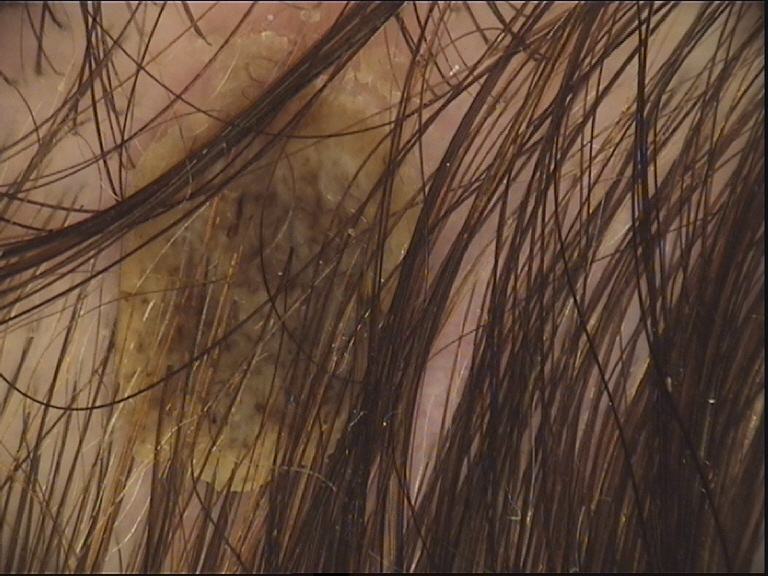The architecture is that of a keratinocytic lesion.
Labeled as a seborrheic keratosis.